A skin lesion imaged with a dermatoscope:
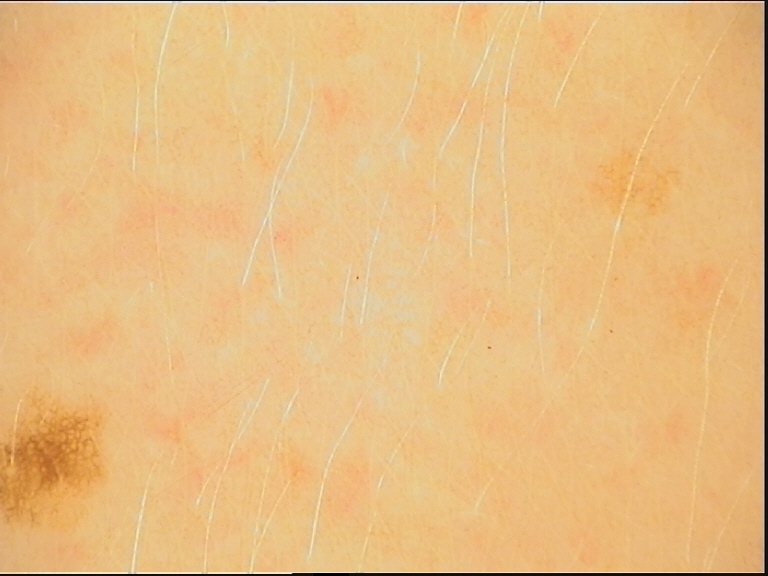Diagnosed as a benign lesion — a dysplastic junctional nevus.